An image taken at an angle.
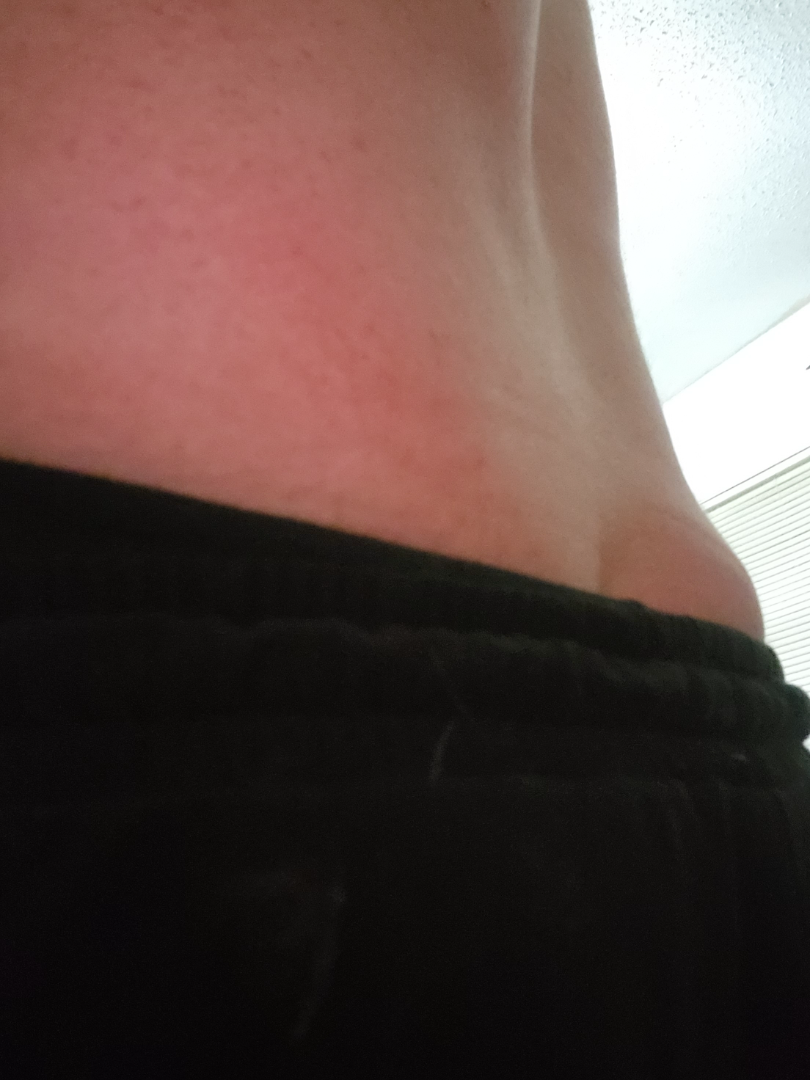<report>
  <assessment>indeterminate</assessment>
</report>